An image taken at a distance.
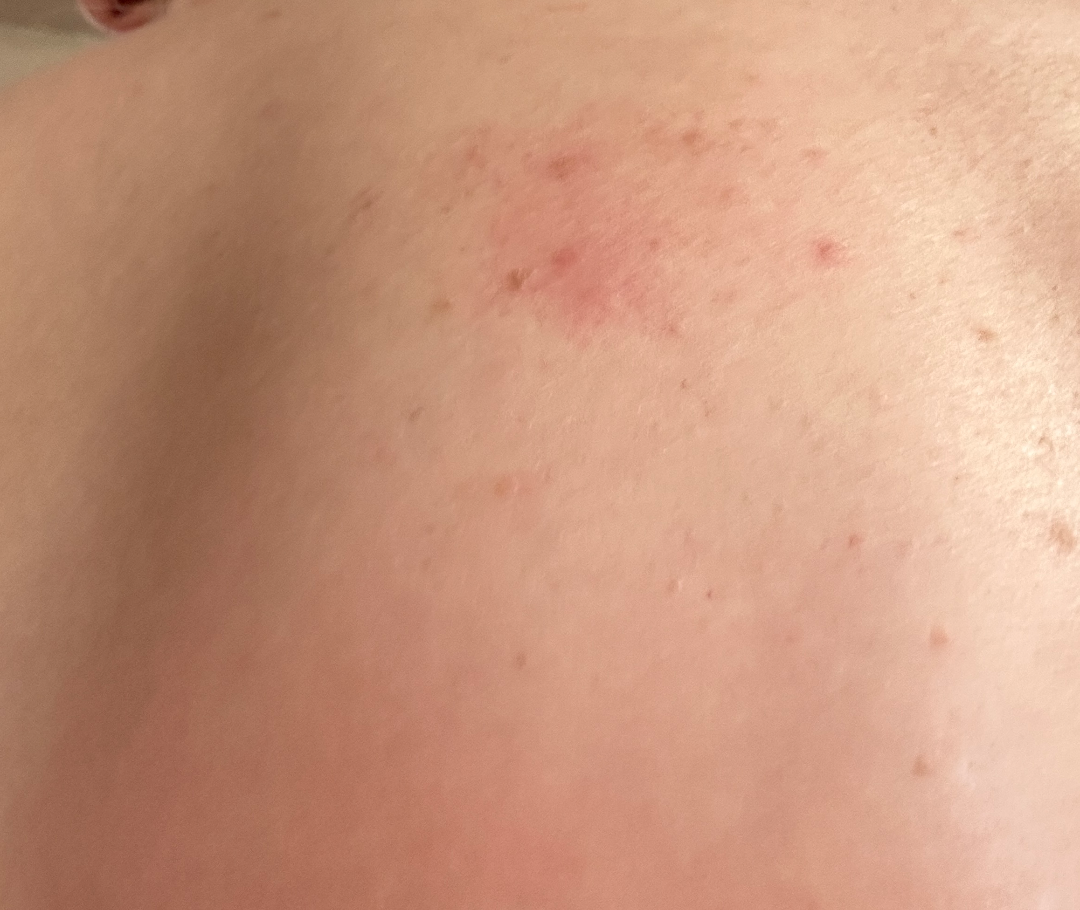Q: What is the patient's skin tone?
A: lay reviewers estimated a Monk skin tone scale of 3
Q: What conditions are considered?
A: one reviewing dermatologist: the favored diagnosis is Allergic Contact Dermatitis; possibly Acne; with consideration of Folliculitis